Recorded as FST III; a male patient aged 38-42; the chart documents melanoma in a first-degree relative: 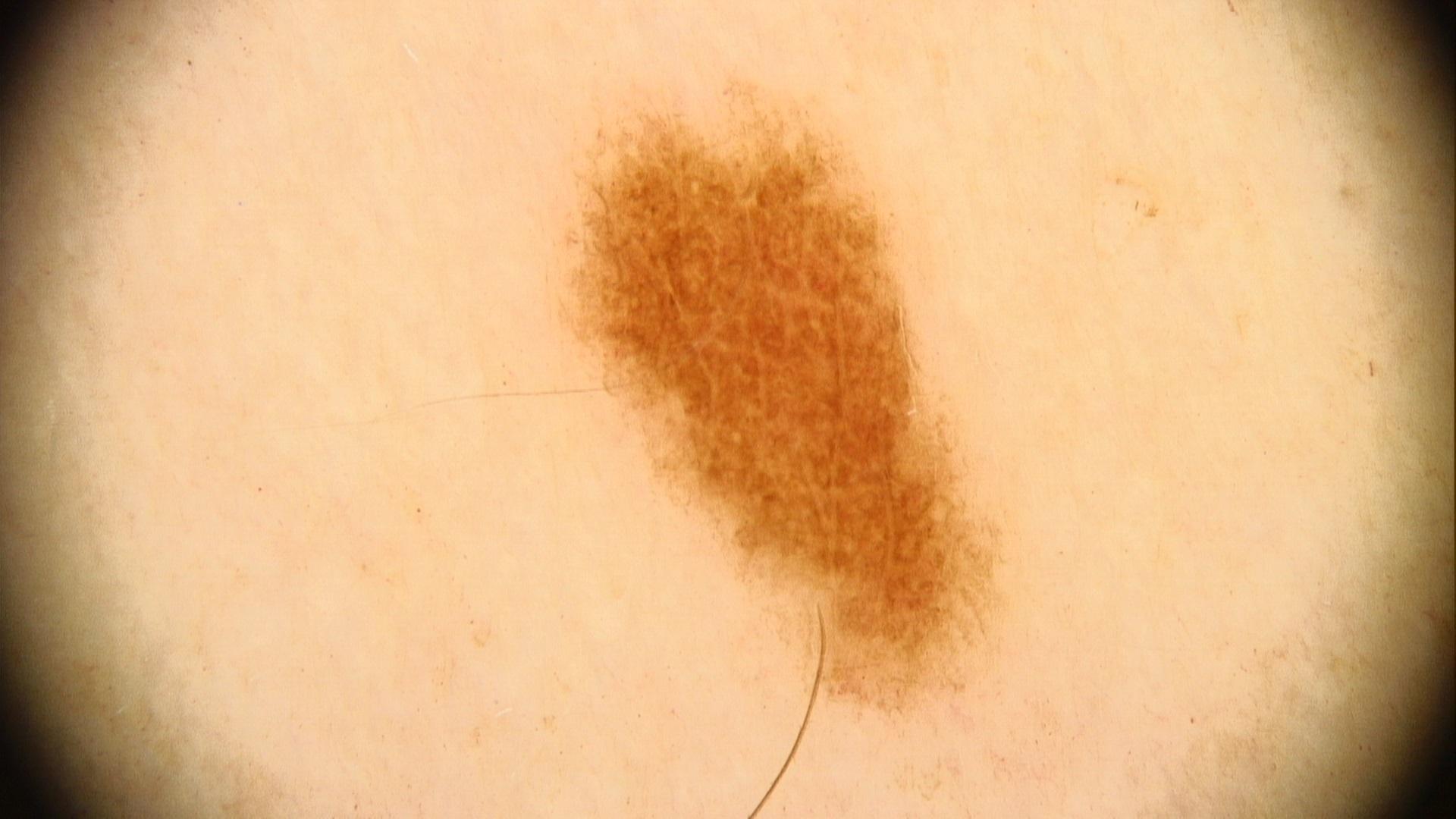Q: Where on the body is the lesion?
A: the trunk (the anterior trunk)
Q: What was the clinical impression?
A: Nevus